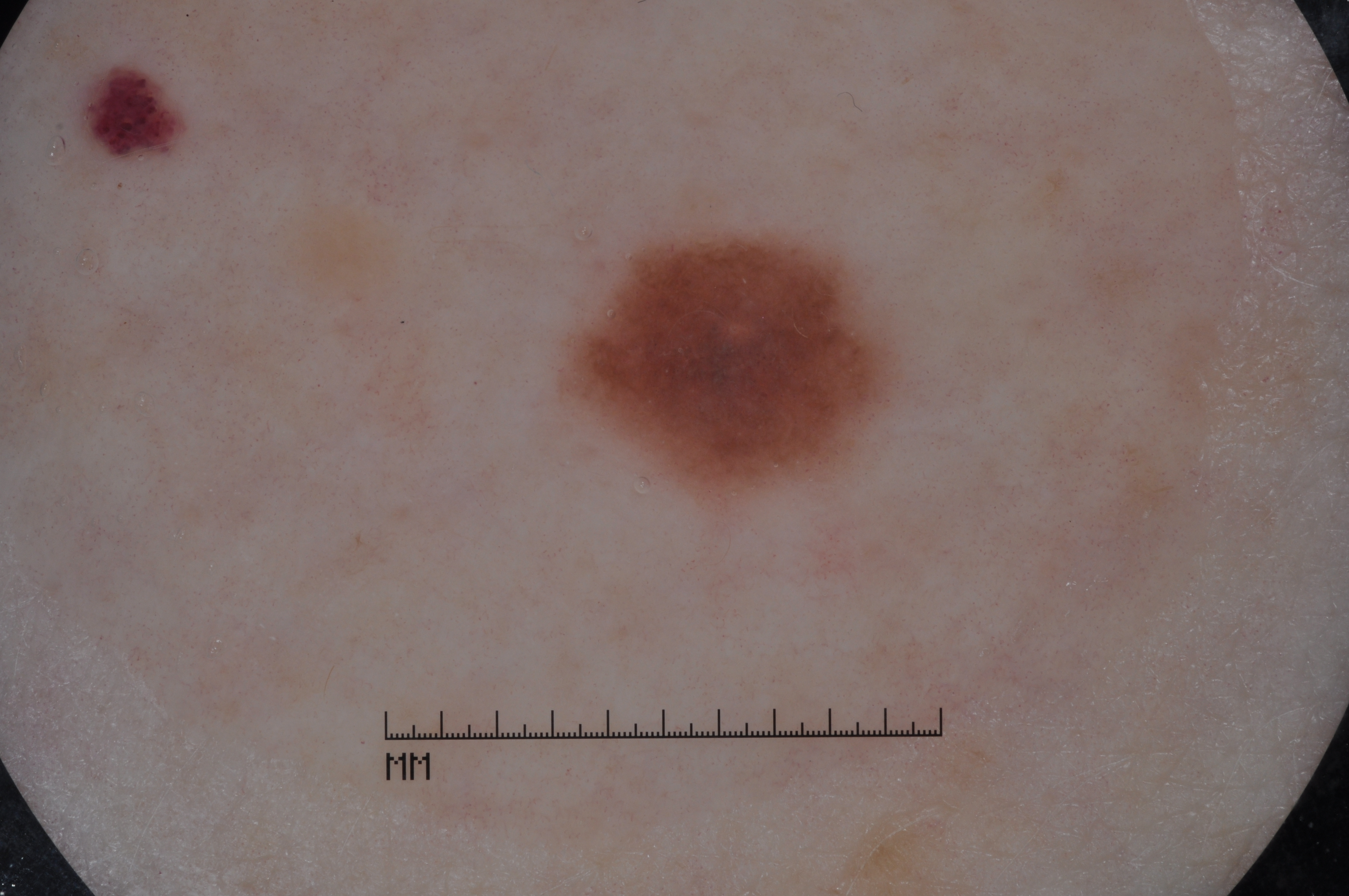image type: dermatoscopic image of a skin lesion; subject: female, aged around 55; features: milia-like cysts; location: [569,231,885,497]; size: ~5% of the field; assessment: a melanocytic nevus, a benign skin lesion.